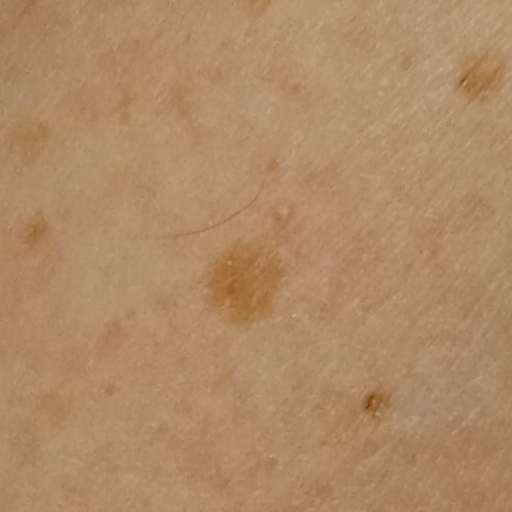clinical context: research study (no referral diagnosis) | sun reaction: skin reddens with sun exposure | nevus count: few melanocytic nevi overall | subject: female, age 71 | risk factors: a personal history of skin cancer, a personal history of cancer, no immunosuppression | body site: an arm | size: 1.7 mm | diagnosis: melanocytic nevus (dermatologist consensus).